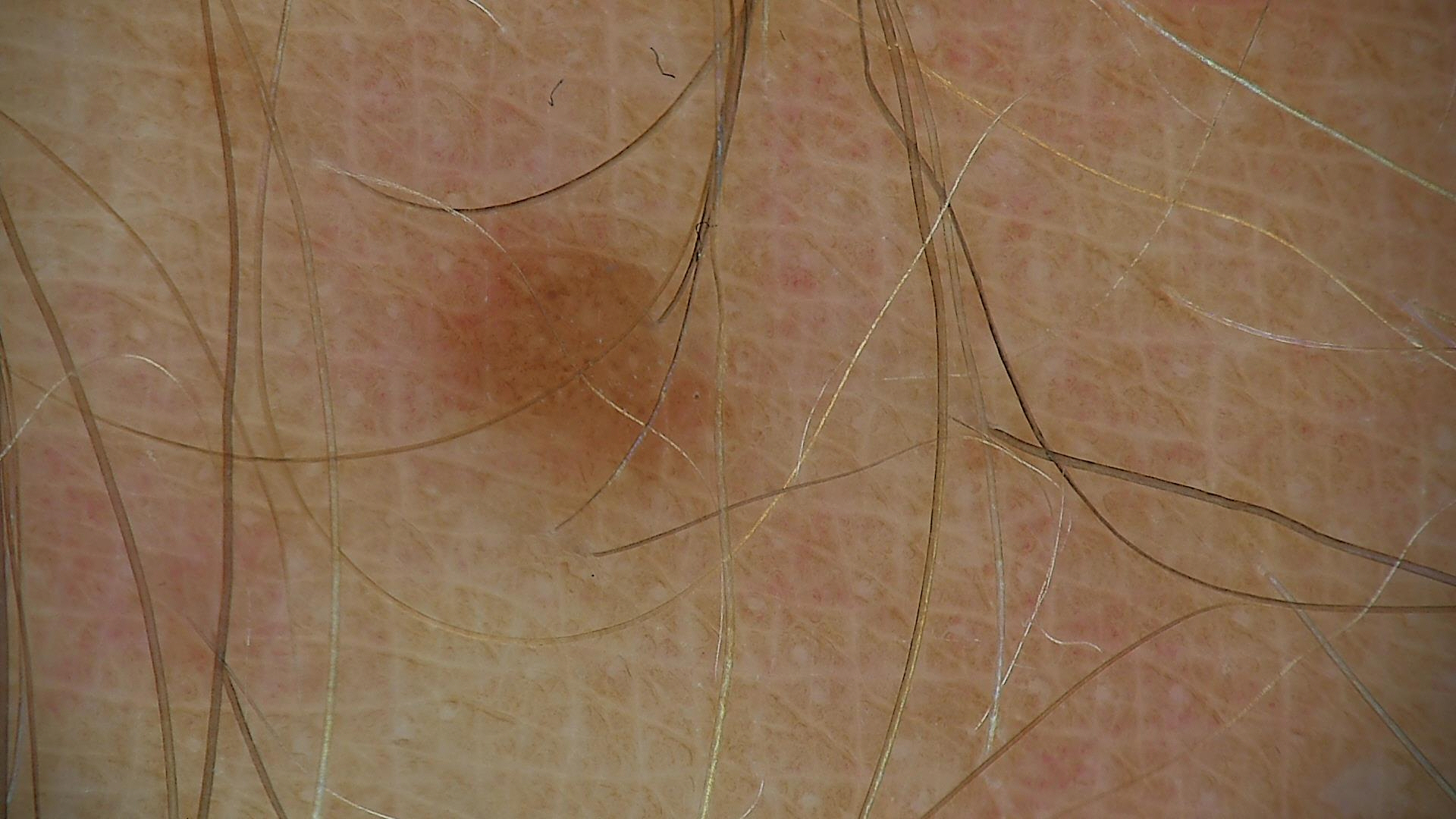Conclusion:
Classified as a junctional nevus.